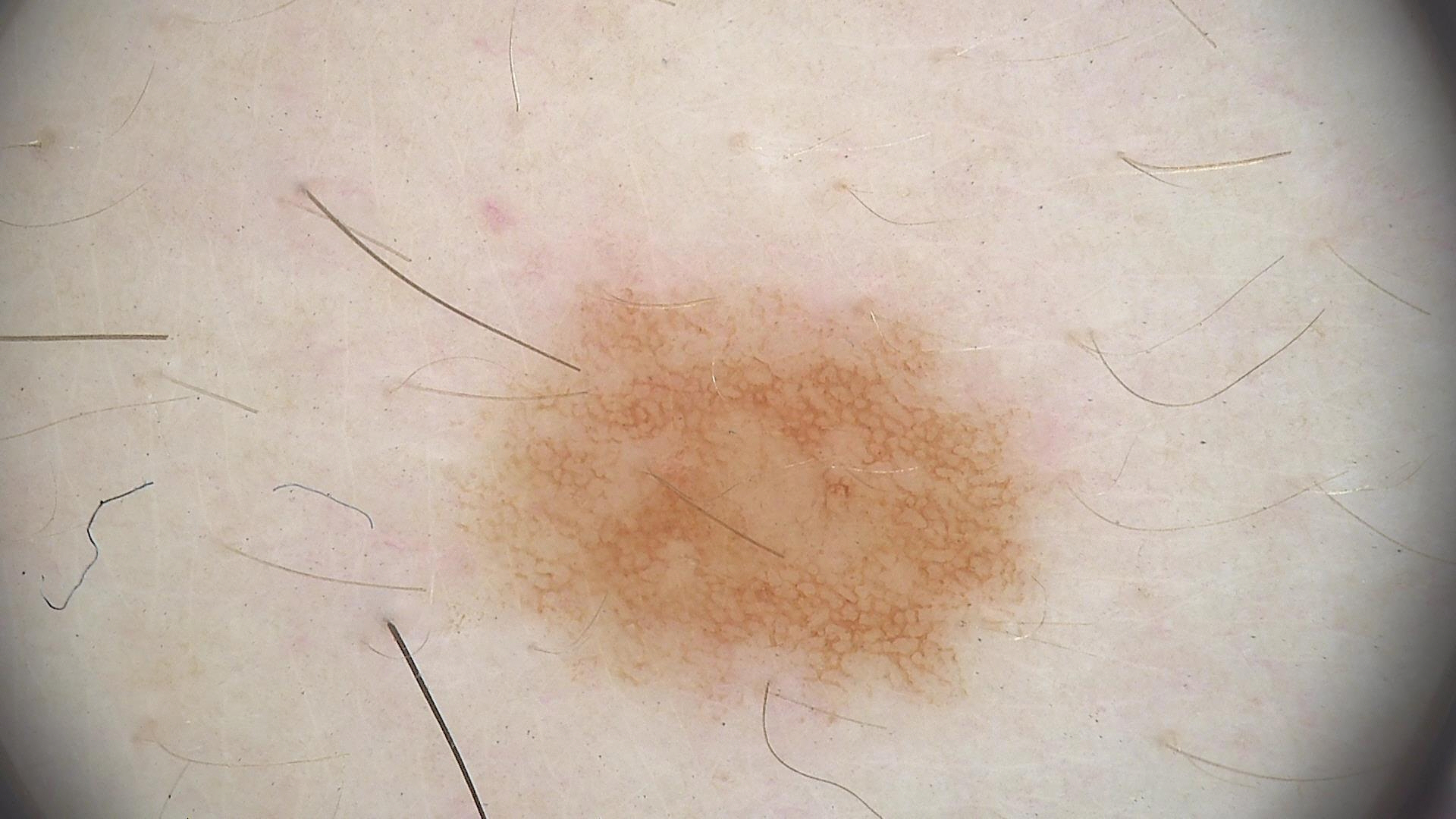Impression:
Labeled as a dysplastic junctional nevus.